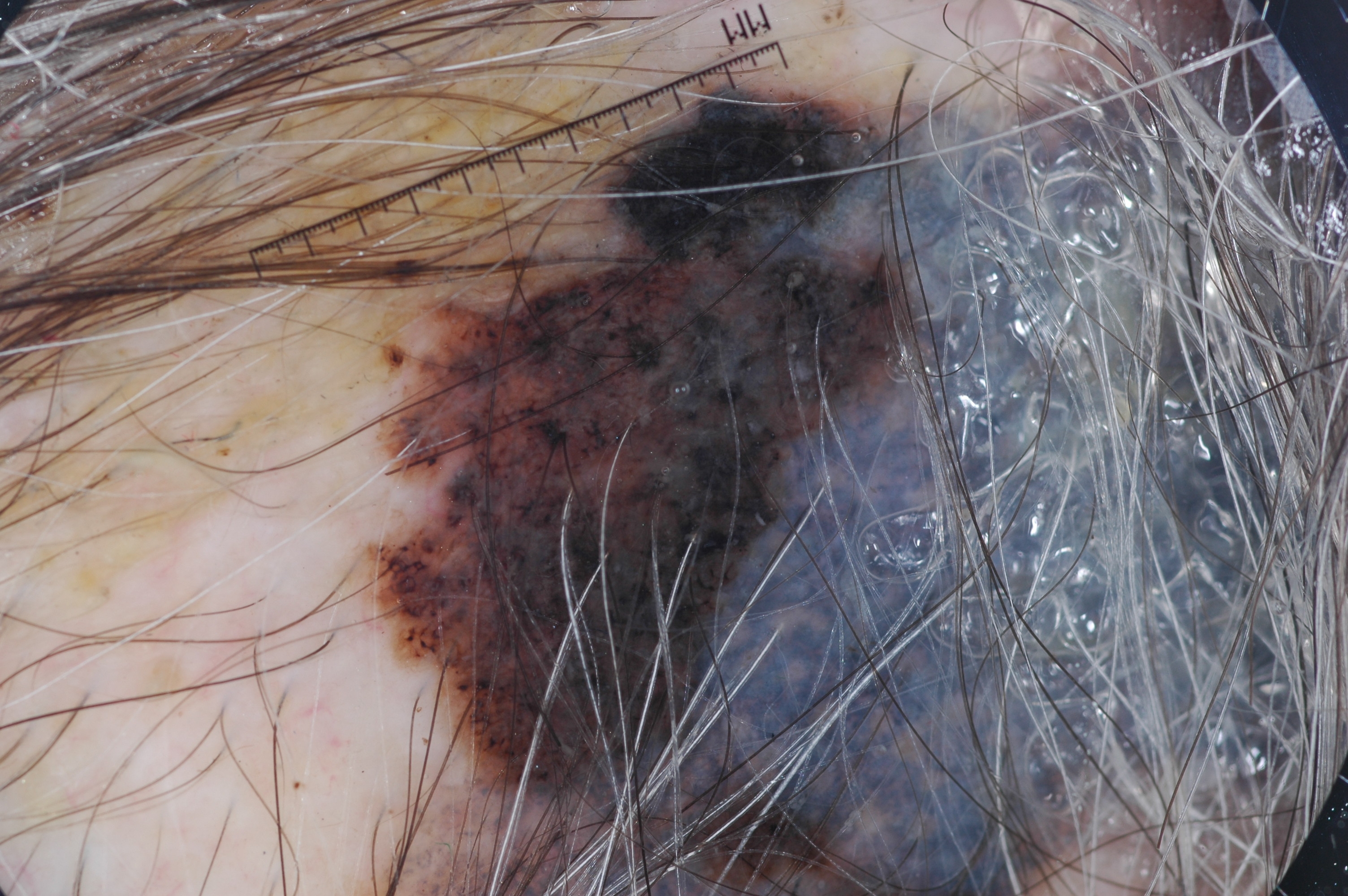patient = male, in their mid- to late 80s or older | imaging = dermatoscopic image of a skin lesion | bounding box = [335, 2, 1339, 893] | dermoscopic findings = pigment network; absent: streaks, negative network, and milia-like cysts | impression = a melanoma.